Reported duration is less than one week · this is a close-up image · female contributor, age 18–29 · located on the leg · the lesion is described as raised or bumpy · the patient considered this a rash · the patient indicates burning, bothersome appearance, itching and enlargement.
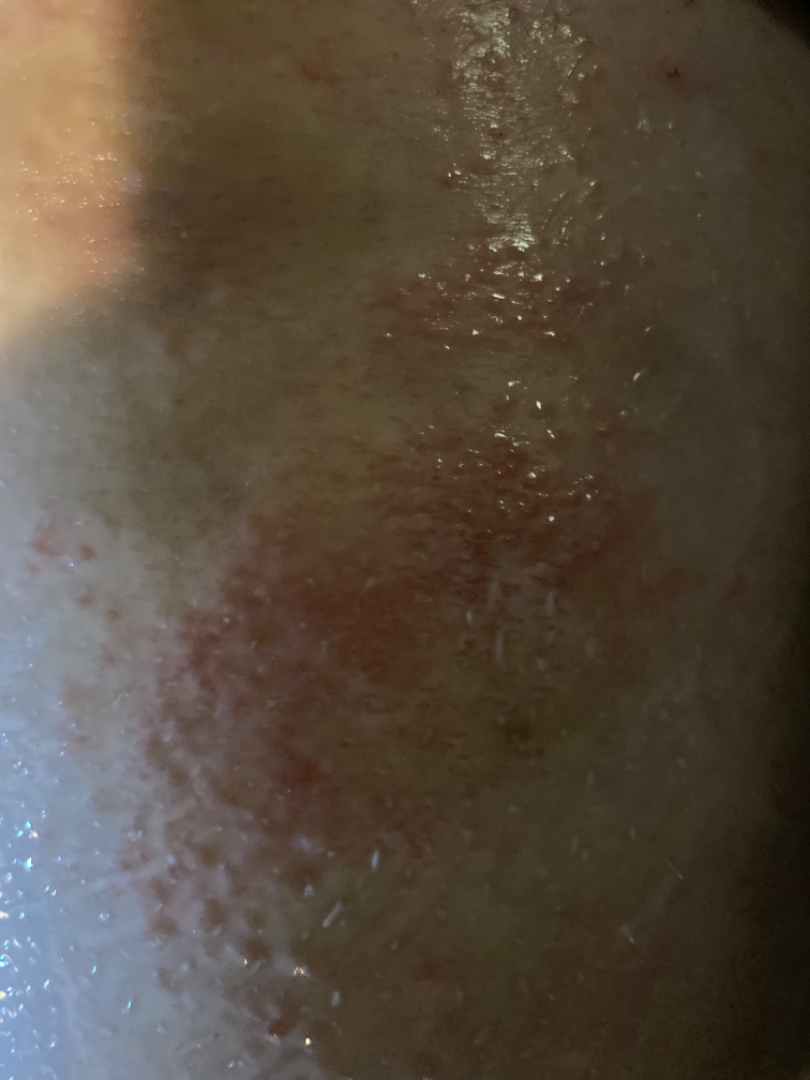differential:
  leading:
    - Eczema
  considered:
    - Contact dermatitis
  unlikely:
    - Allergic Contact Dermatitis
    - Darier's disease
    - Hailey Hailey disease